Dermoscopy of a skin lesion. FST II. A male subject about 65 years old.
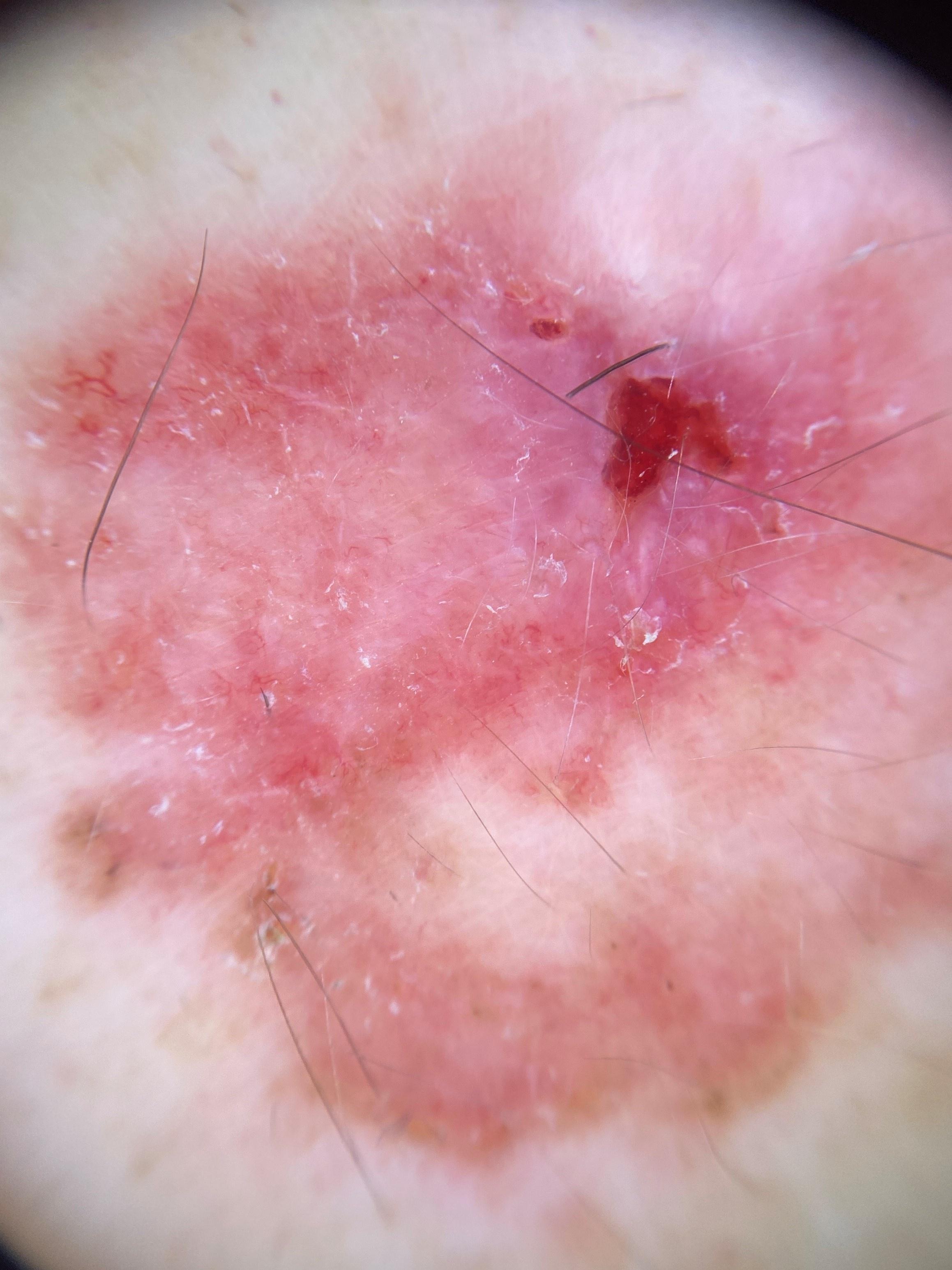Findings:
The lesion is on the anterior trunk.
Diagnosis:
Biopsy-confirmed as a basal cell carcinoma.